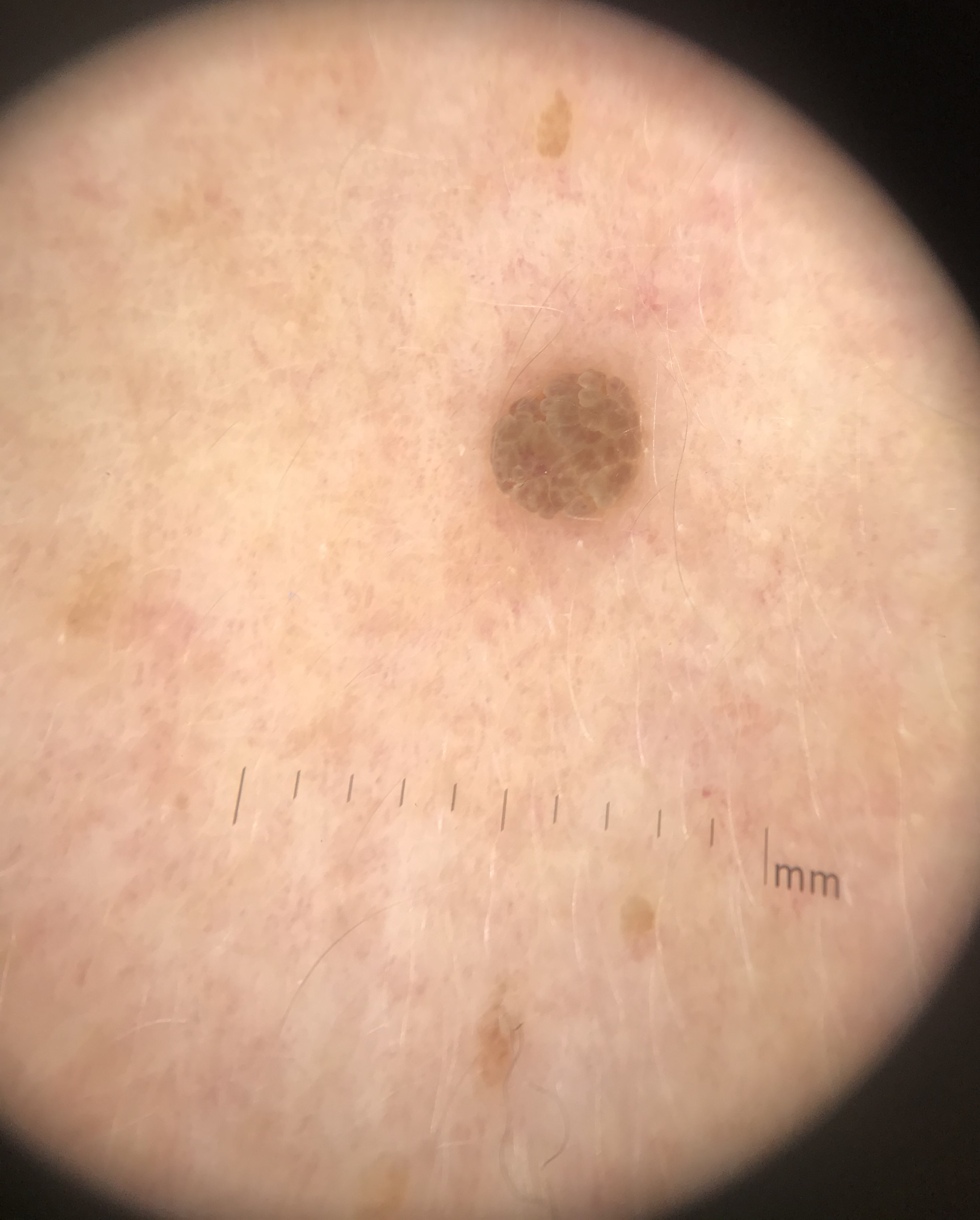Q: What is the lesion category?
A: keratinocytic
Q: What is the diagnosis?
A: seborrheic keratosis (expert consensus)